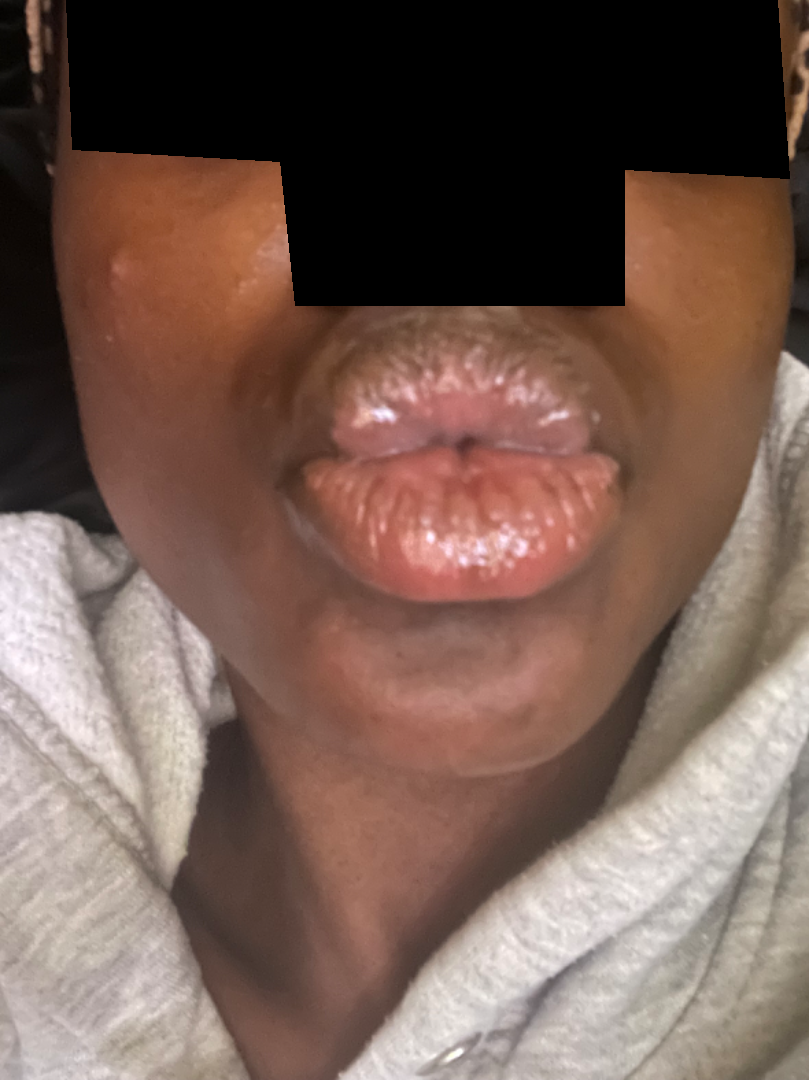patient: female, age 18–29
symptoms:
  - itching
  - burning
  - bothersome appearance
shot_type: close-up
patient_category: acne
body_site:
  - sole of the foot
  - top or side of the foot
  - back of the hand
duration: about one day
texture:
  - raised or bumpy
  - fluid-filled